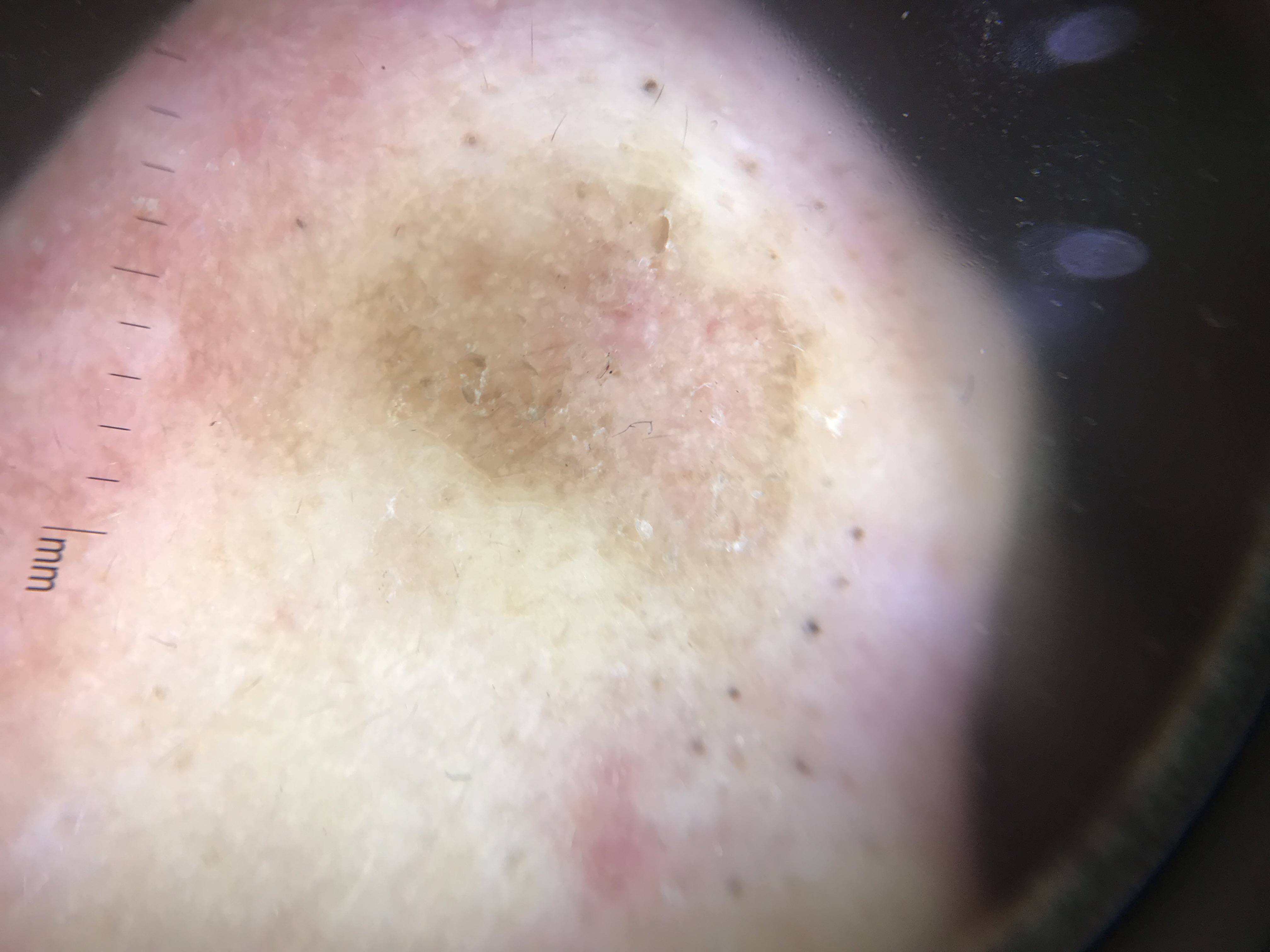Q: What is the imaging modality?
A: dermoscopy
Q: What was the diagnostic impression?
A: seborrheic keratosis (expert consensus)